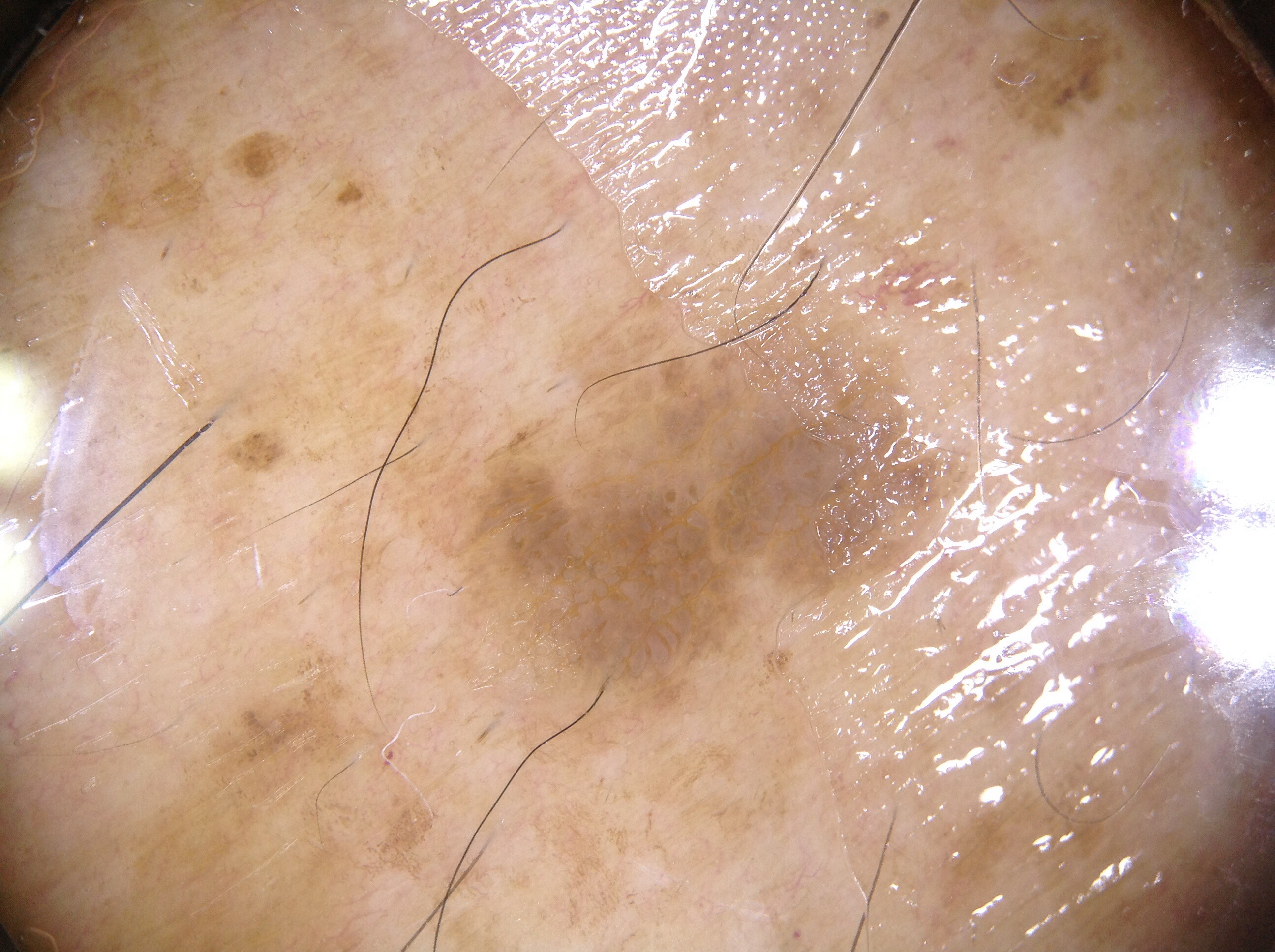The patient is a male aged approximately 80.
A dermoscopy image of a single skin lesion.
A moderately sized lesion.
The lesion's extent is 309 211 986 776.
Dermoscopic review identifies no streaks, negative network, pigment network, or milia-like cysts.
The lesion was assessed as a seborrheic keratosis, a benign skin lesion.